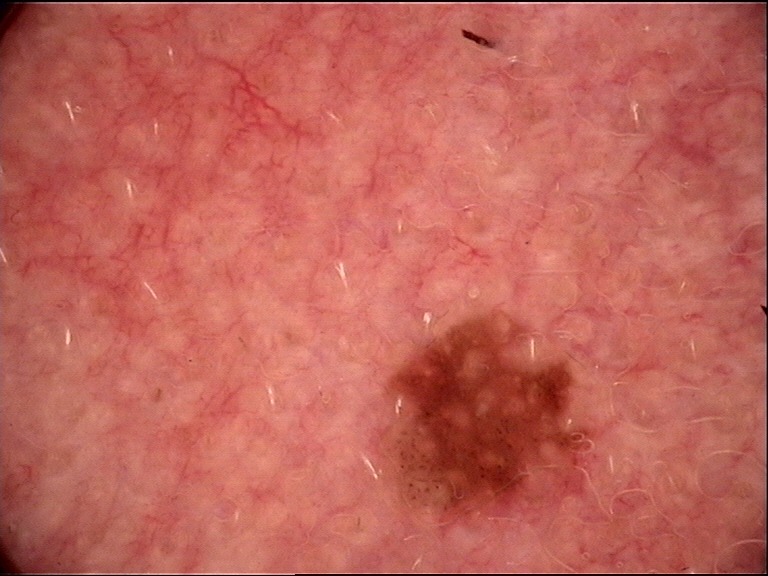image = dermoscopy, diagnosis = Miescher nevus (expert consensus).